The subject is a female approximately 40 years of age, a dermatoscopic image of a skin lesion — 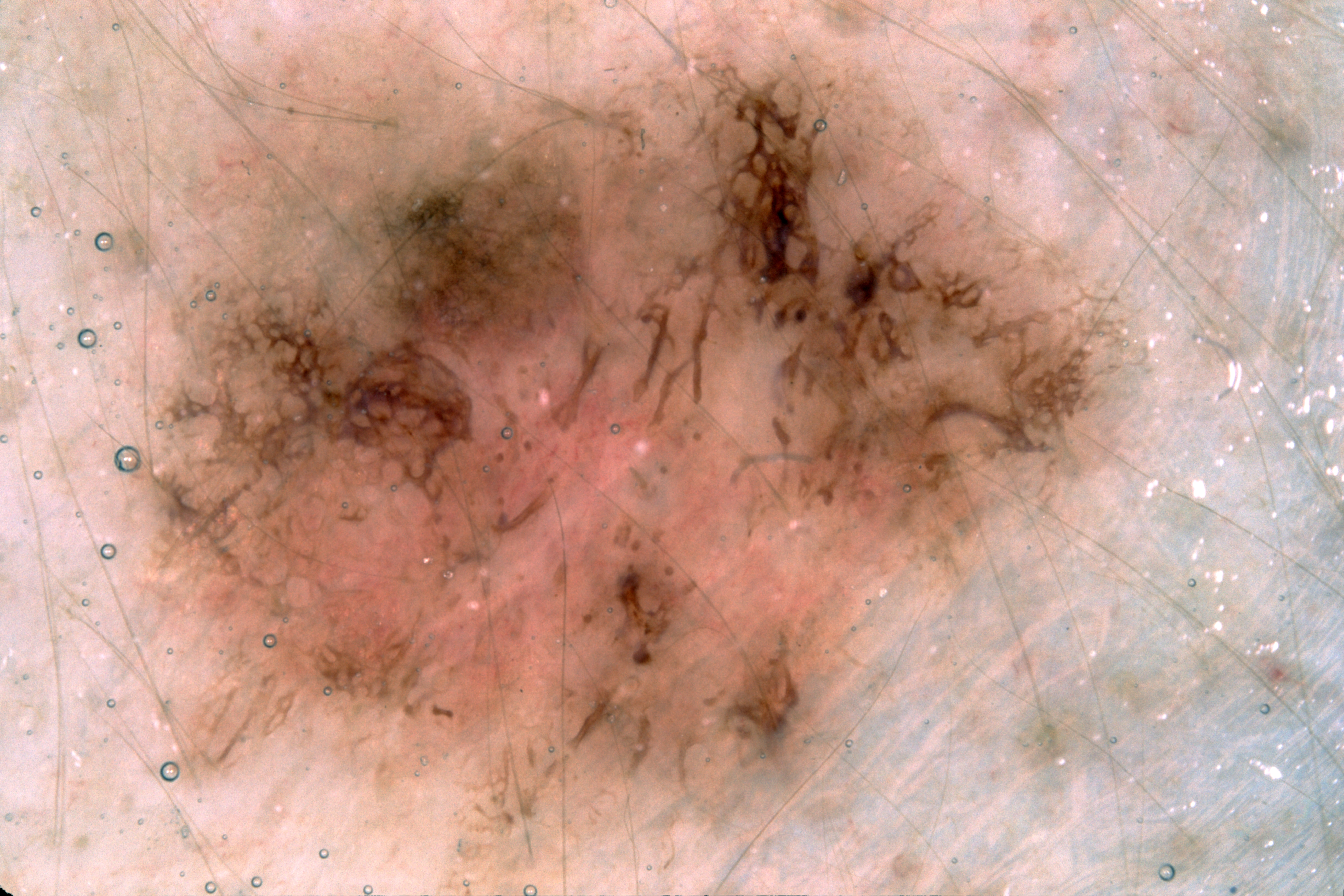| field | value |
|---|---|
| lesion bbox | x1=115, y1=21, x2=1123, y2=895 |
| dermoscopic findings | pigment network and milia-like cysts; absent: streaks and negative network |
| assessment | a melanoma |